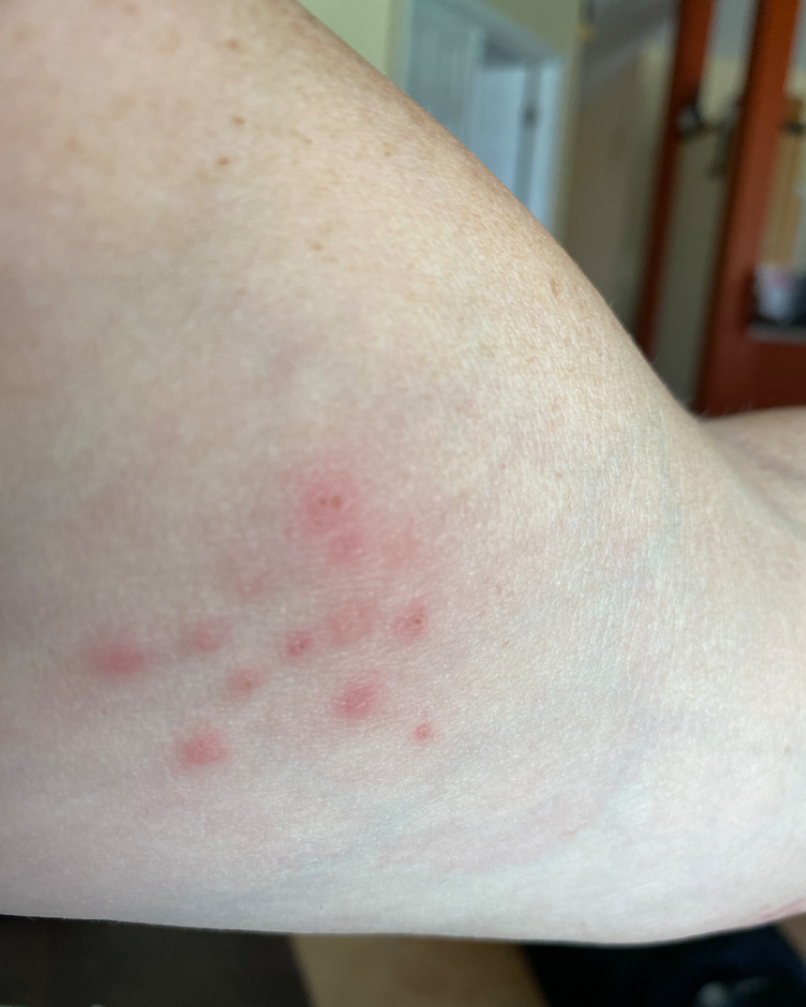location: arm | view: close-up | impression: most consistent with Insect Bite; also on the differential is Herpes Simplex; less probable is Allergic Contact Dermatitis.